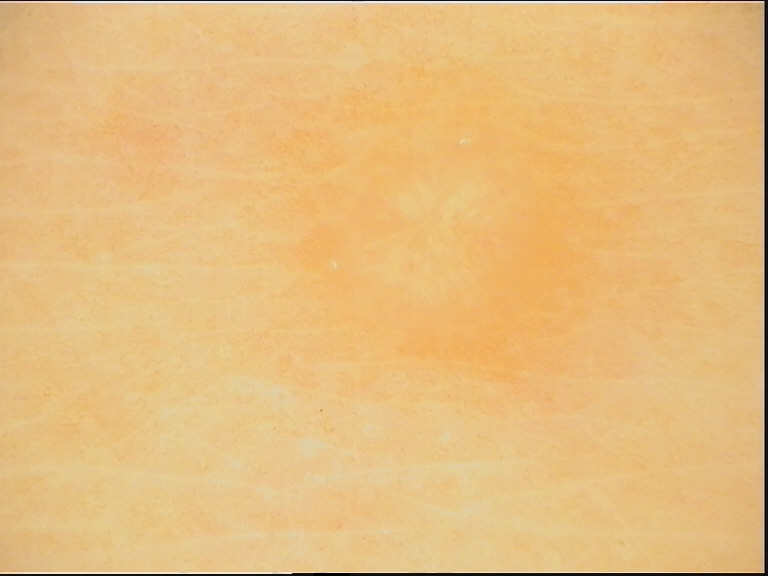Impression:
Classified as a dermatofibroma.